A female subject, in their mid- to late 50s; a dermoscopic close-up of a skin lesion:
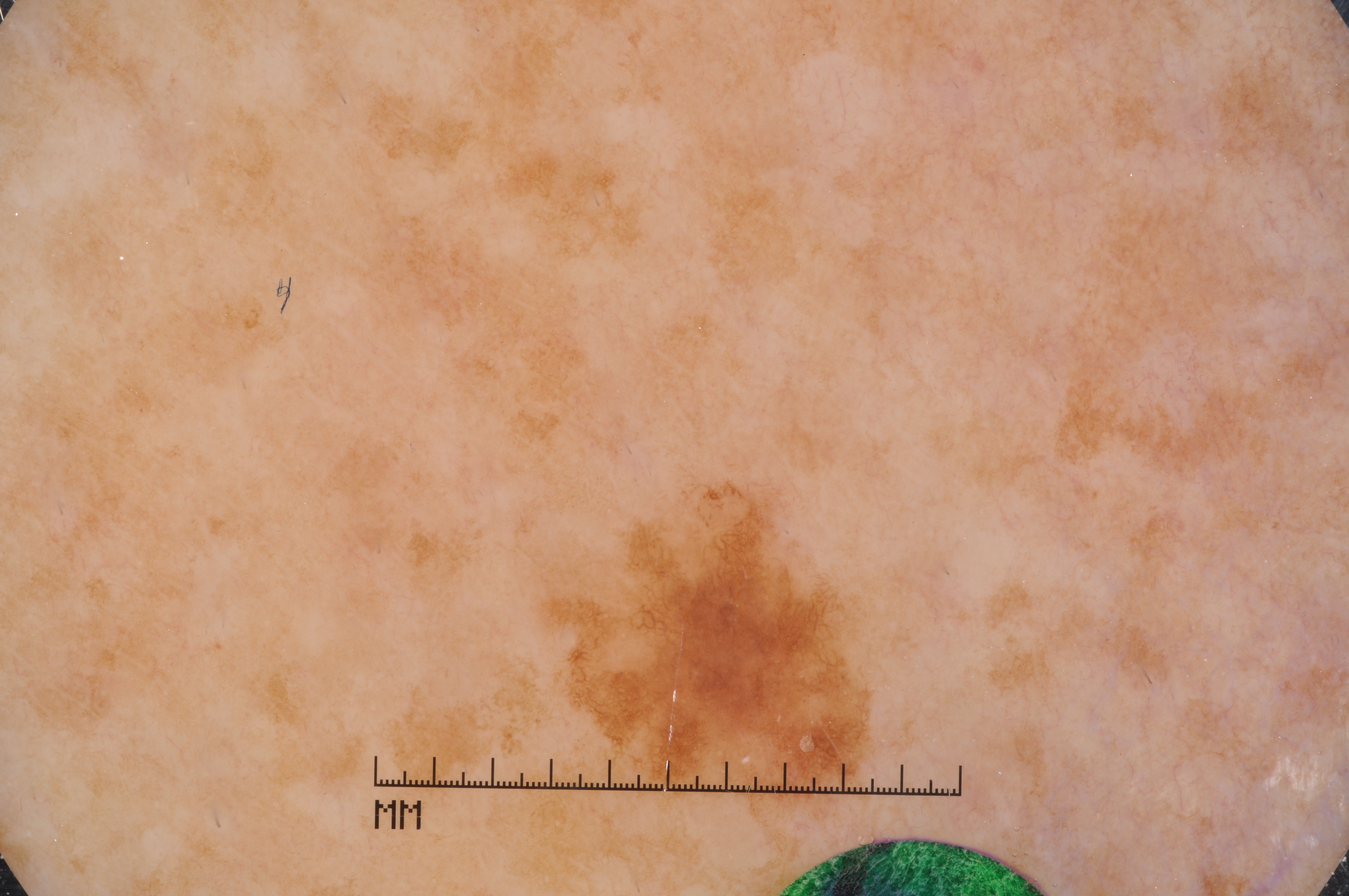As (left, top, right, bottom), lesion location: box(569, 490, 864, 805). Dermoscopic assessment notes pigment network and milia-like cysts; no negative network or streaks. The lesion occupies roughly 5% of the field. Diagnosed as a melanocytic nevus, a benign skin lesion.